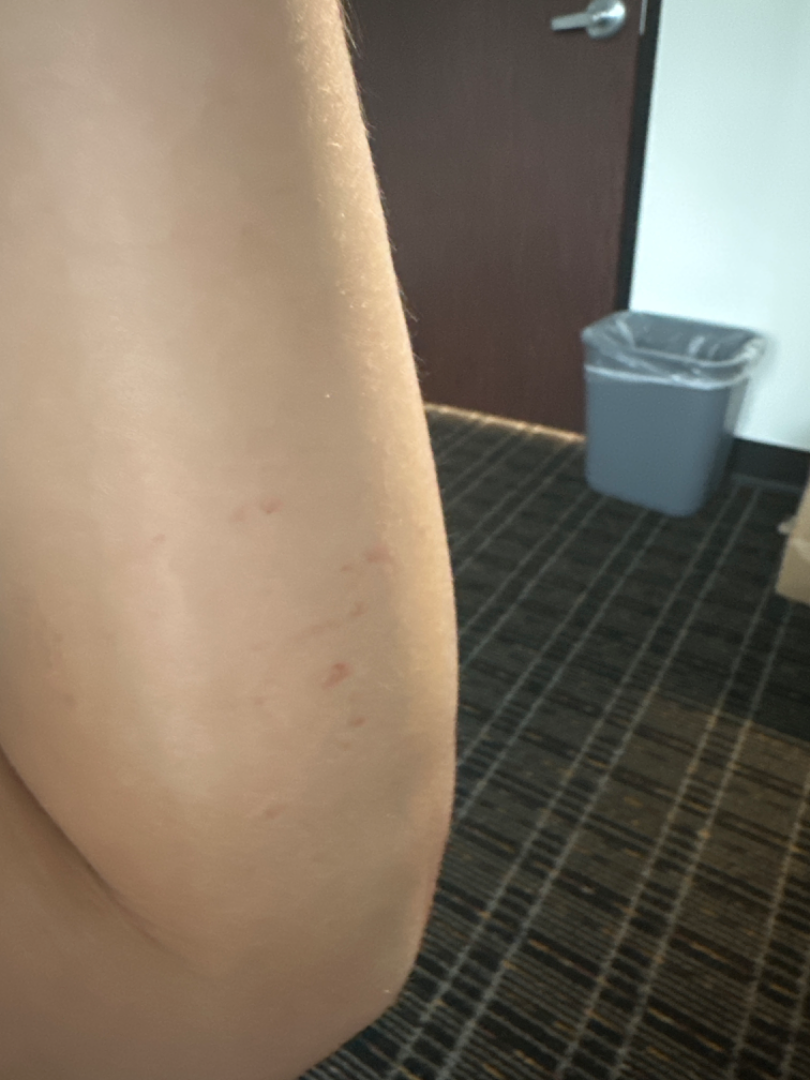assessment — ungradable on photographic review.